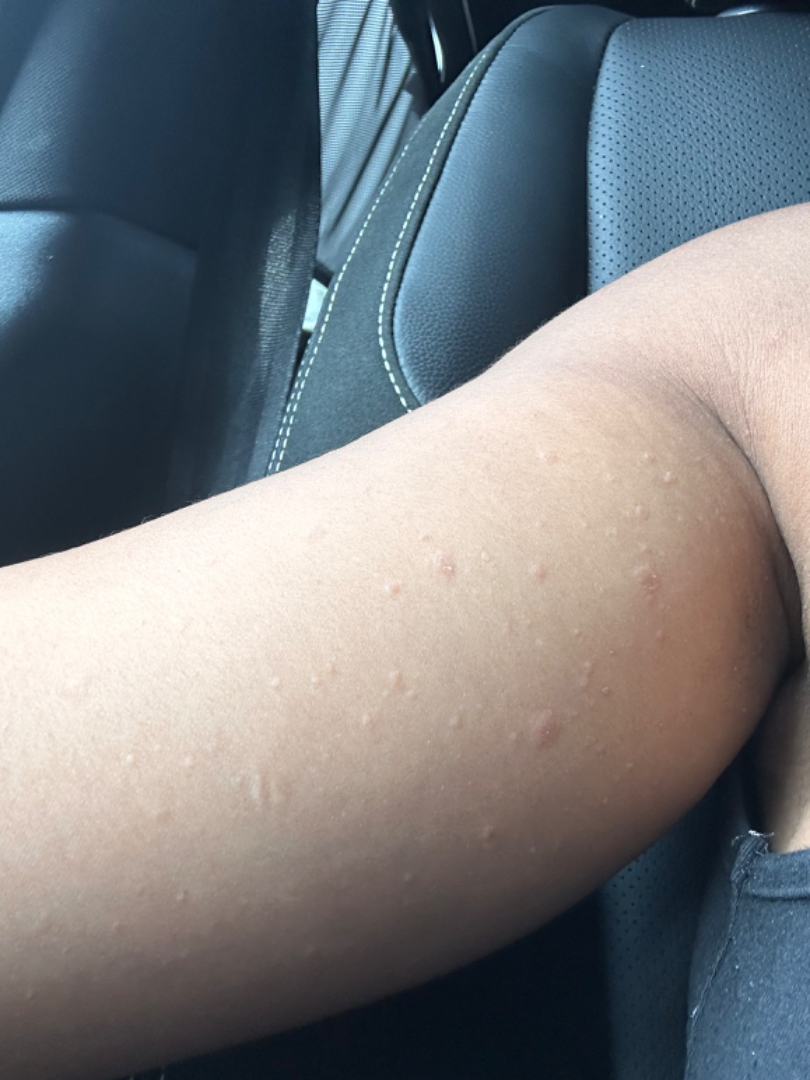| field | value |
|---|---|
| photo taken | close-up |
| symptom duration | one to four weeks |
| affected area | arm |
| dermatologist impression | the leading consideration is Pityriasis rosea; an alternative is Small plaque parapsoriasis; less probable is Syphilis |